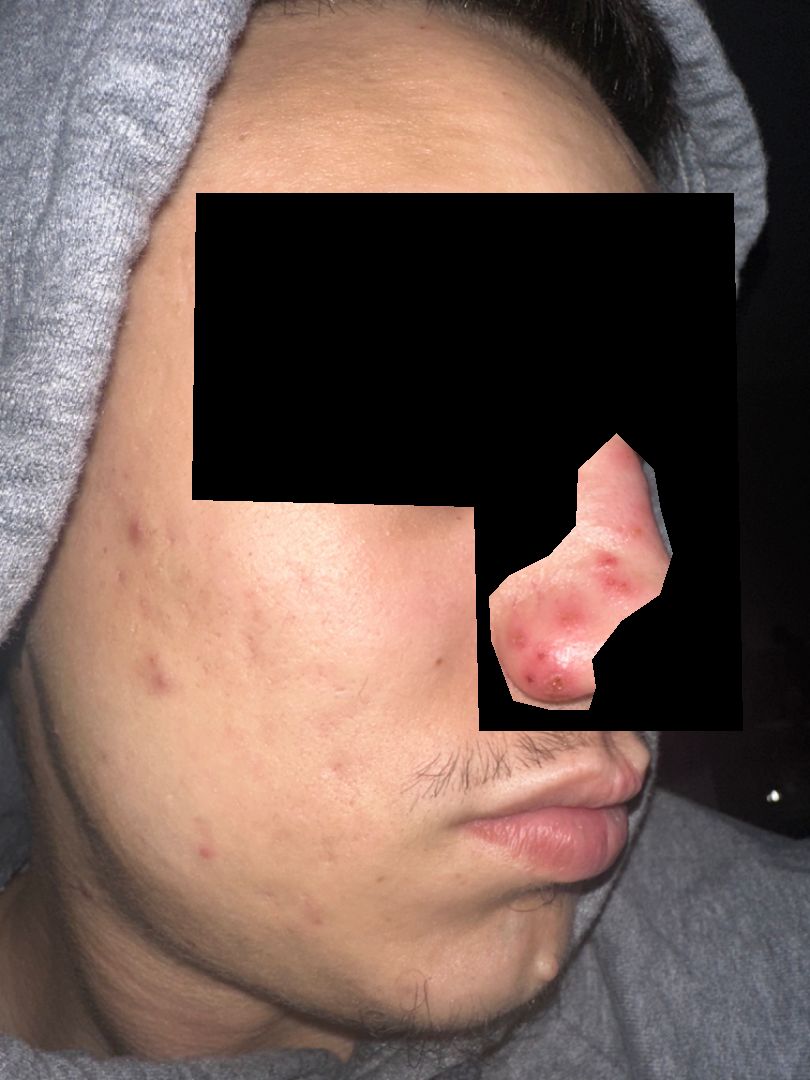The patient indicates itching and pain. Reported duration is less than one week. The subject is a male aged 18–29. The patient indicates the lesion is fluid-filled and rough or flaky. A close-up photograph. Skin tone: FST III.